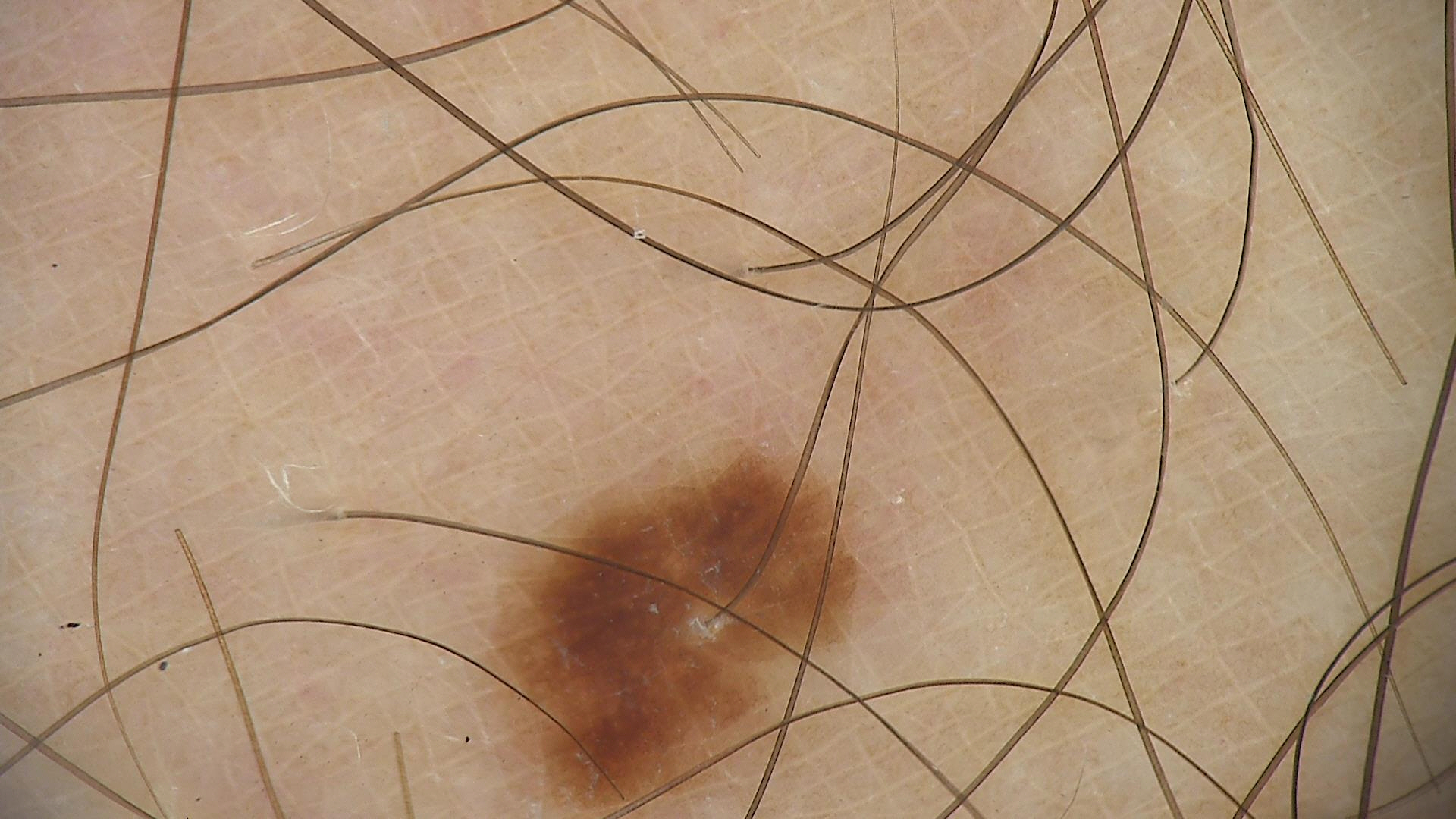Consistent with a dysplastic junctional nevus.